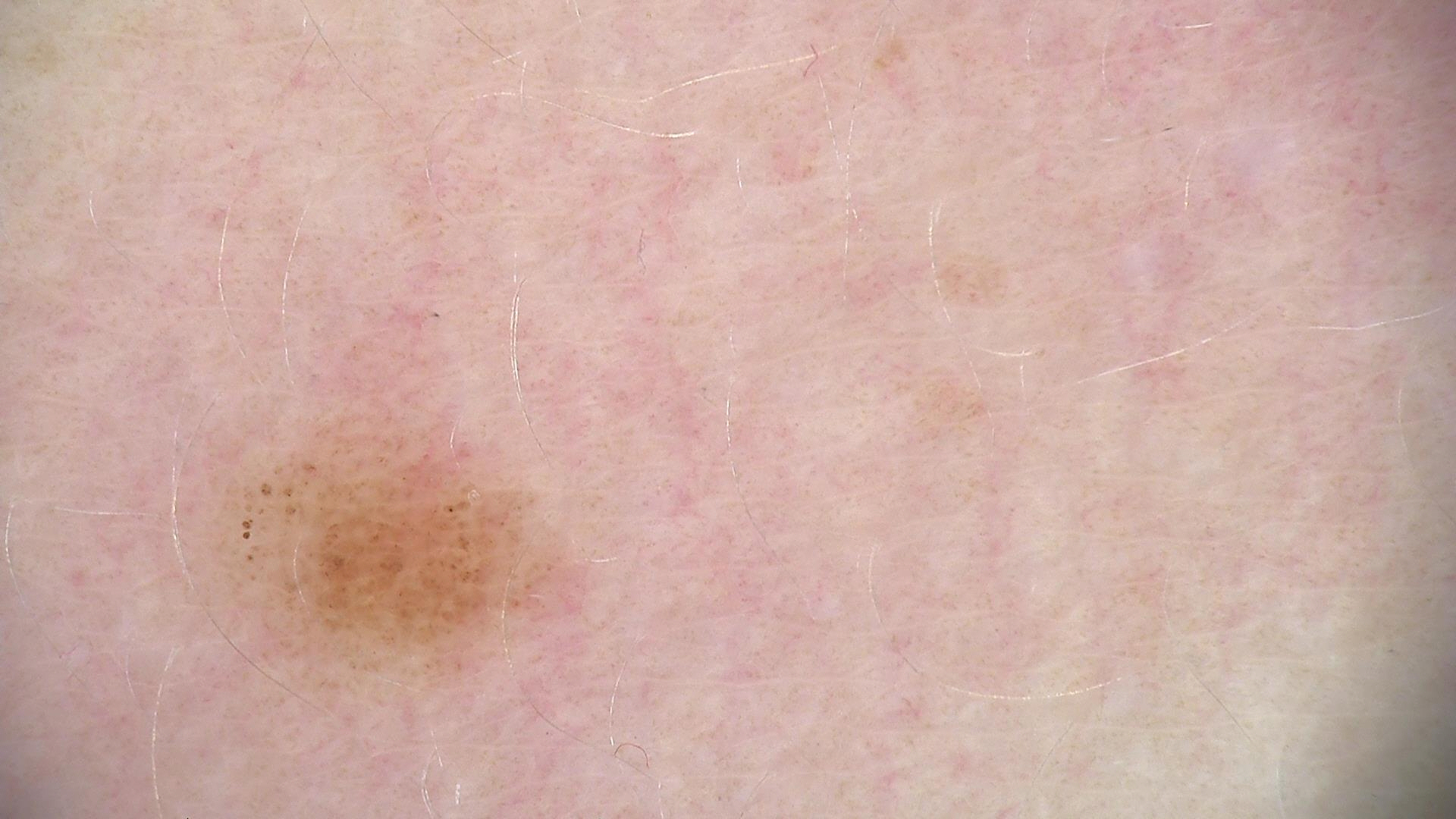Q: What is this lesion?
A: dysplastic junctional nevus (expert consensus)